Located on the head or neck. This image was taken at an angle. Female patient, age 18–29:
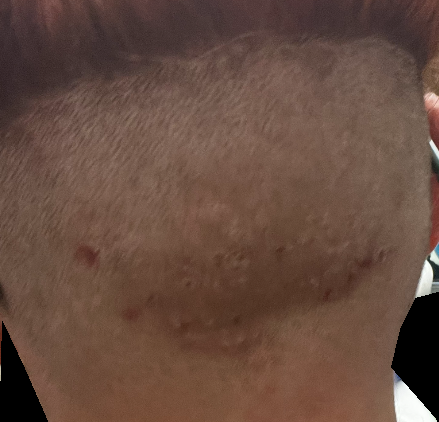differential diagnosis = the leading consideration is Acne keloidalis.